Present for one to three months; the photograph was taken at a distance; the head or neck is involved; the contributor reports bleeding, burning, pain and bothersome appearance; the patient described the issue as a rash — 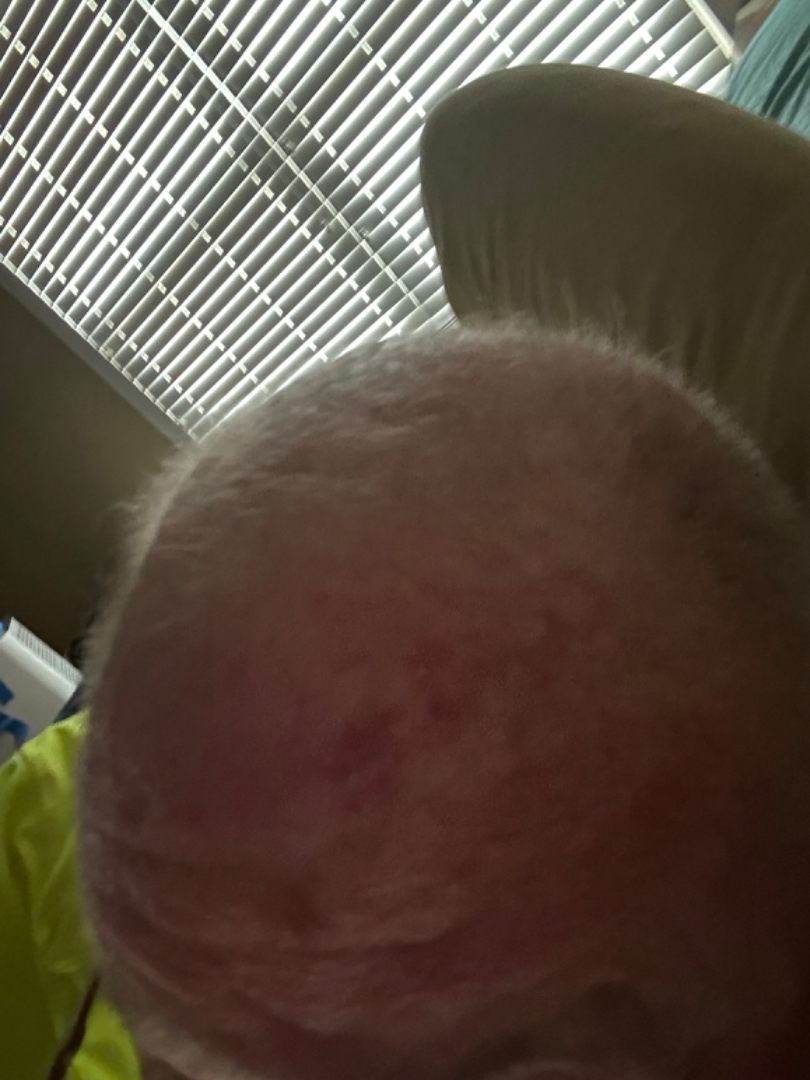{"assessment": "could not be assessed"}